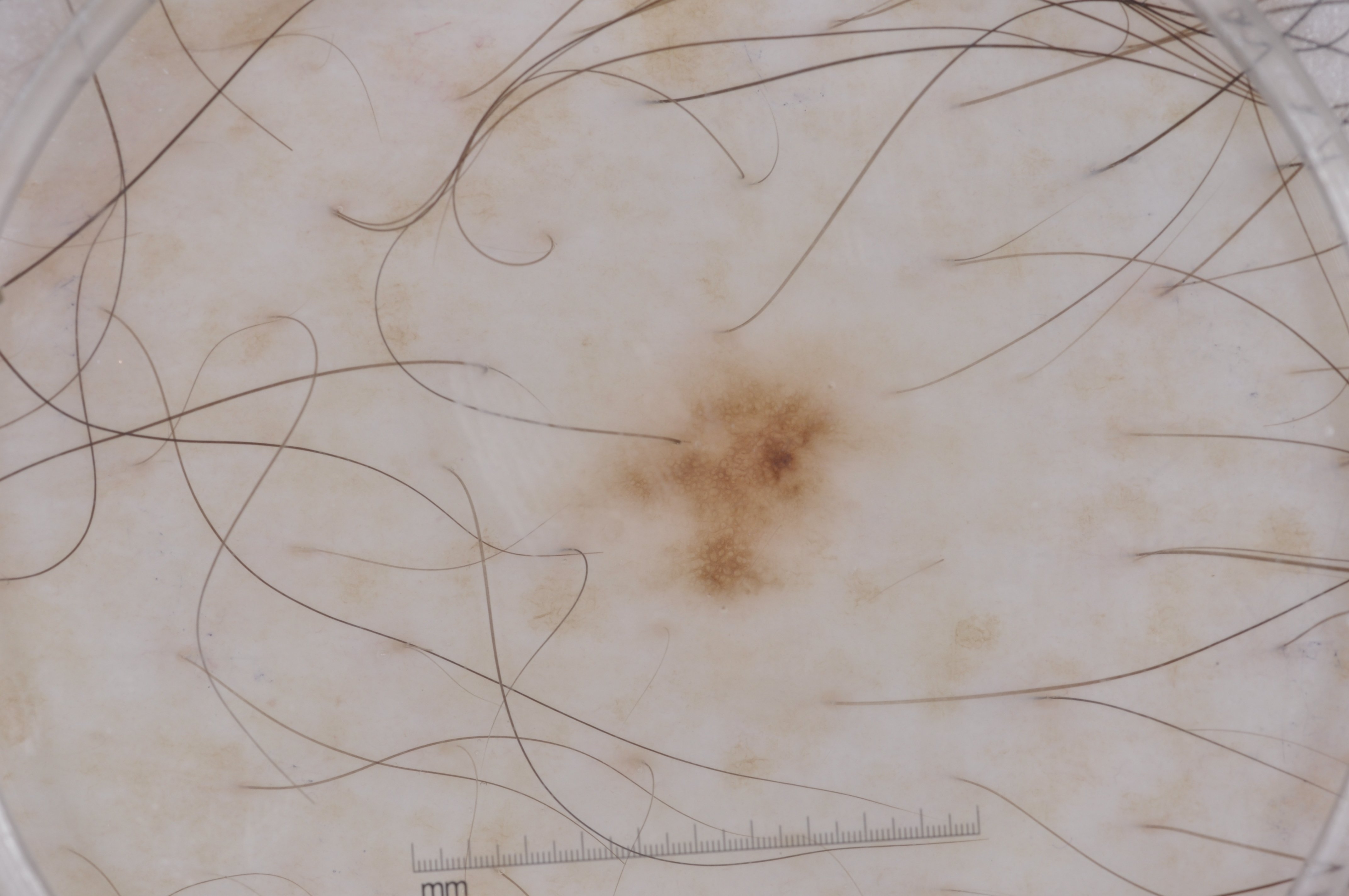A dermoscopic view of a skin lesion. Lesion location: x1=590 y1=343 x2=875 y2=595. Clinically diagnosed as a melanocytic nevus.